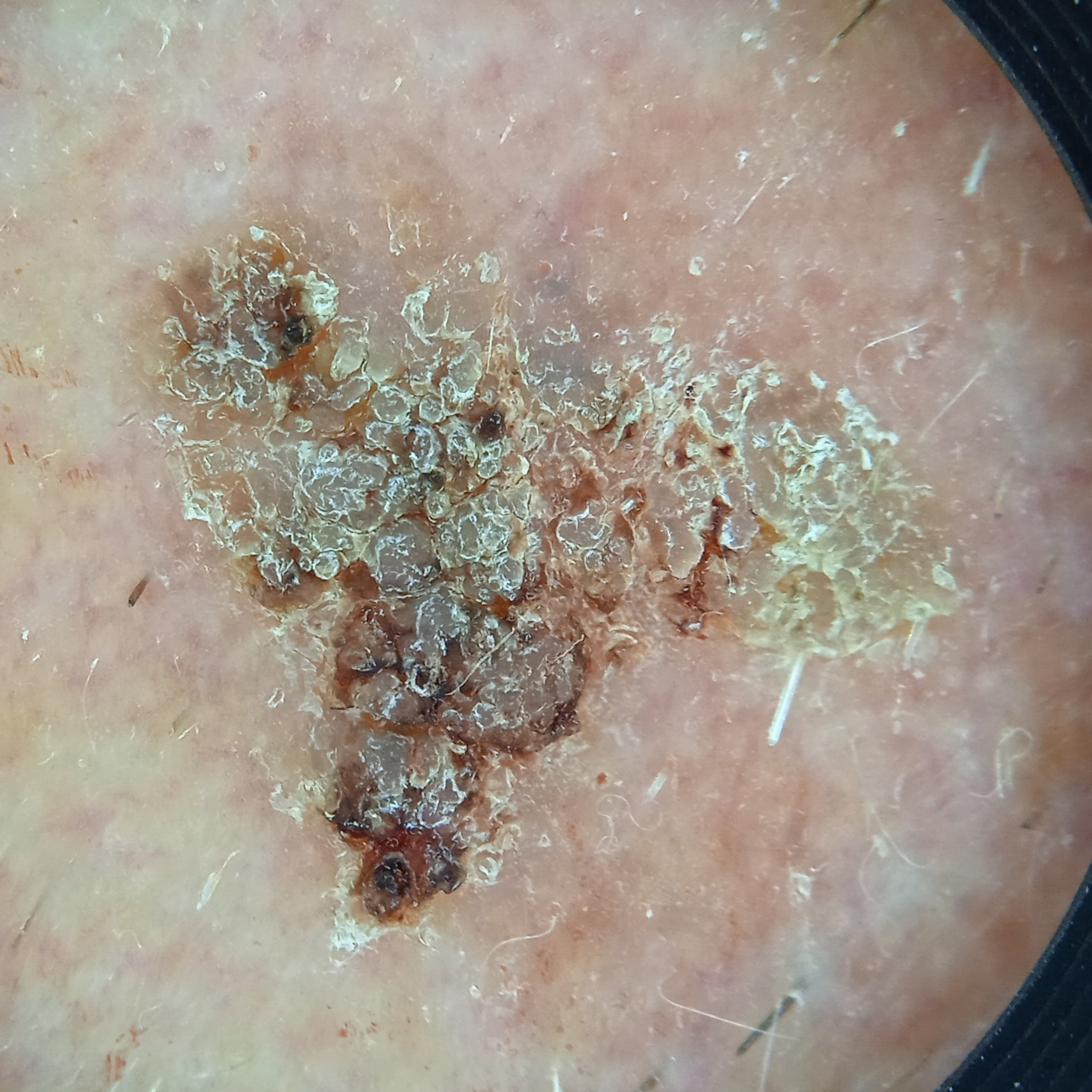On a questionnaire the patient reported a personal history of cancer and no personal history of skin cancer.
A dermoscopic image of a skin lesion.
Few moles overall by the patient's own estimate.
A male patient age 78.
Measuring roughly 10.5 mm.
The dermatologists' assessment was a seborrheic keratosis.